This is a close-up image — 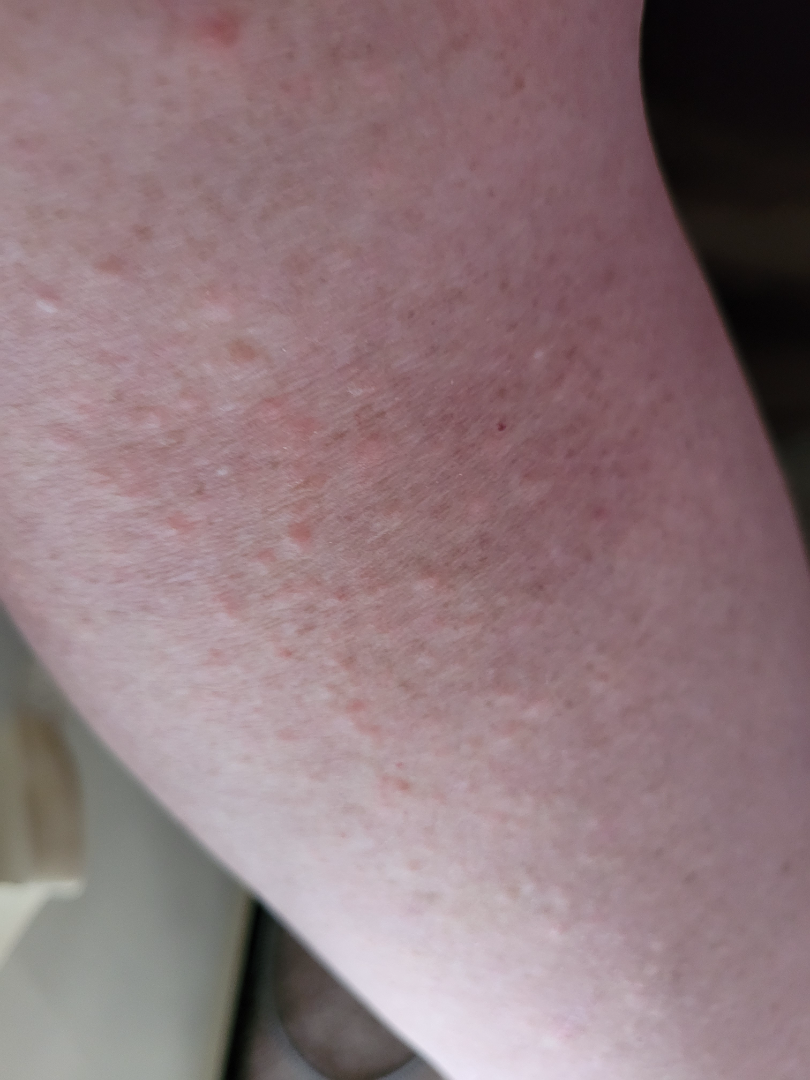• diagnostic considerations: most consistent with Eczema; the differential also includes Lichen Simplex Chronicus